A dermoscopic close-up of a skin lesion — 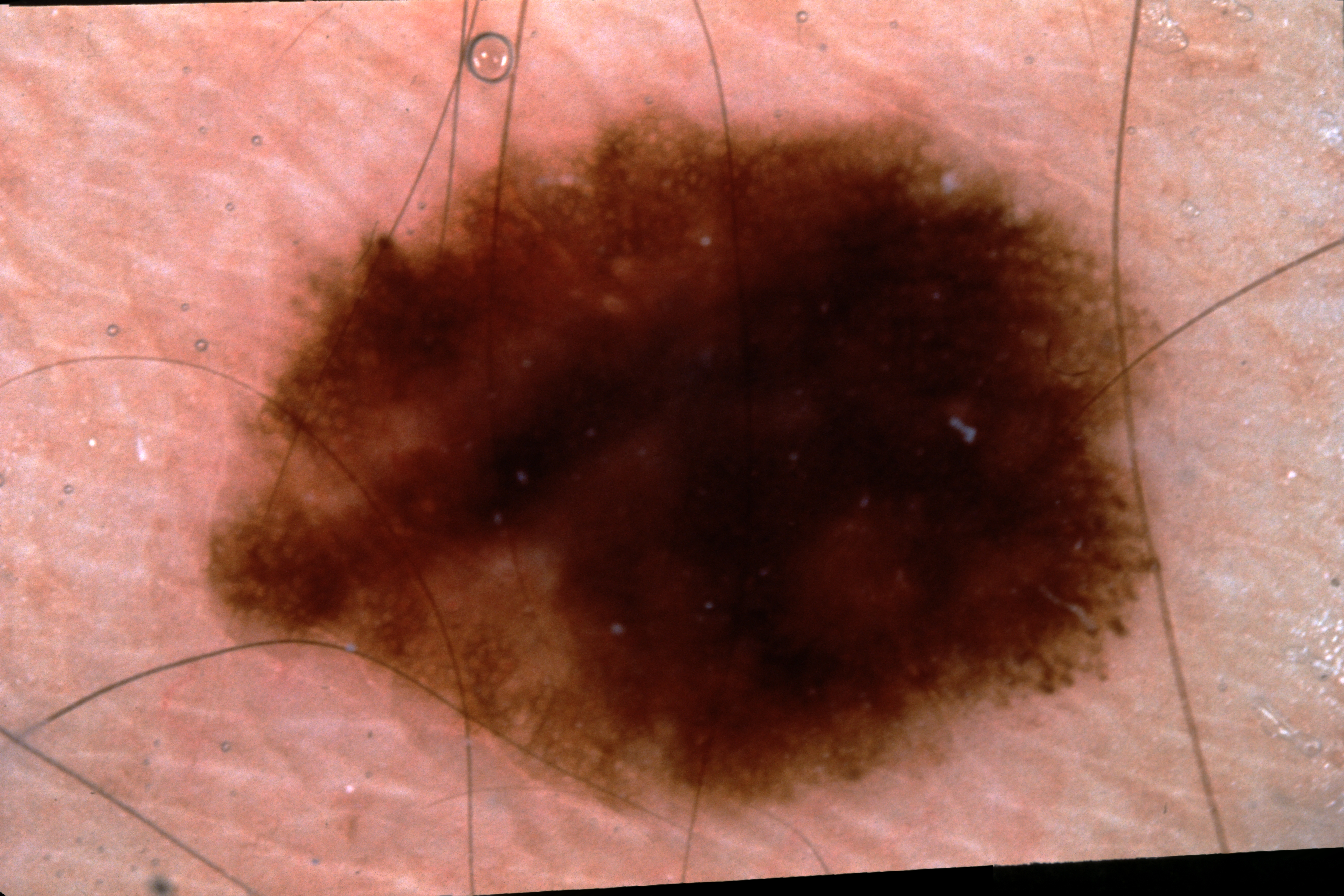Case summary:
A large lesion occupying much of the field. On dermoscopy, the lesion shows pigment network and streaks; no negative network or milia-like cysts. The lesion is bounded by x1=173, y1=103, x2=1176, y2=823.
Conclusion:
The biopsy diagnosis was a melanoma.